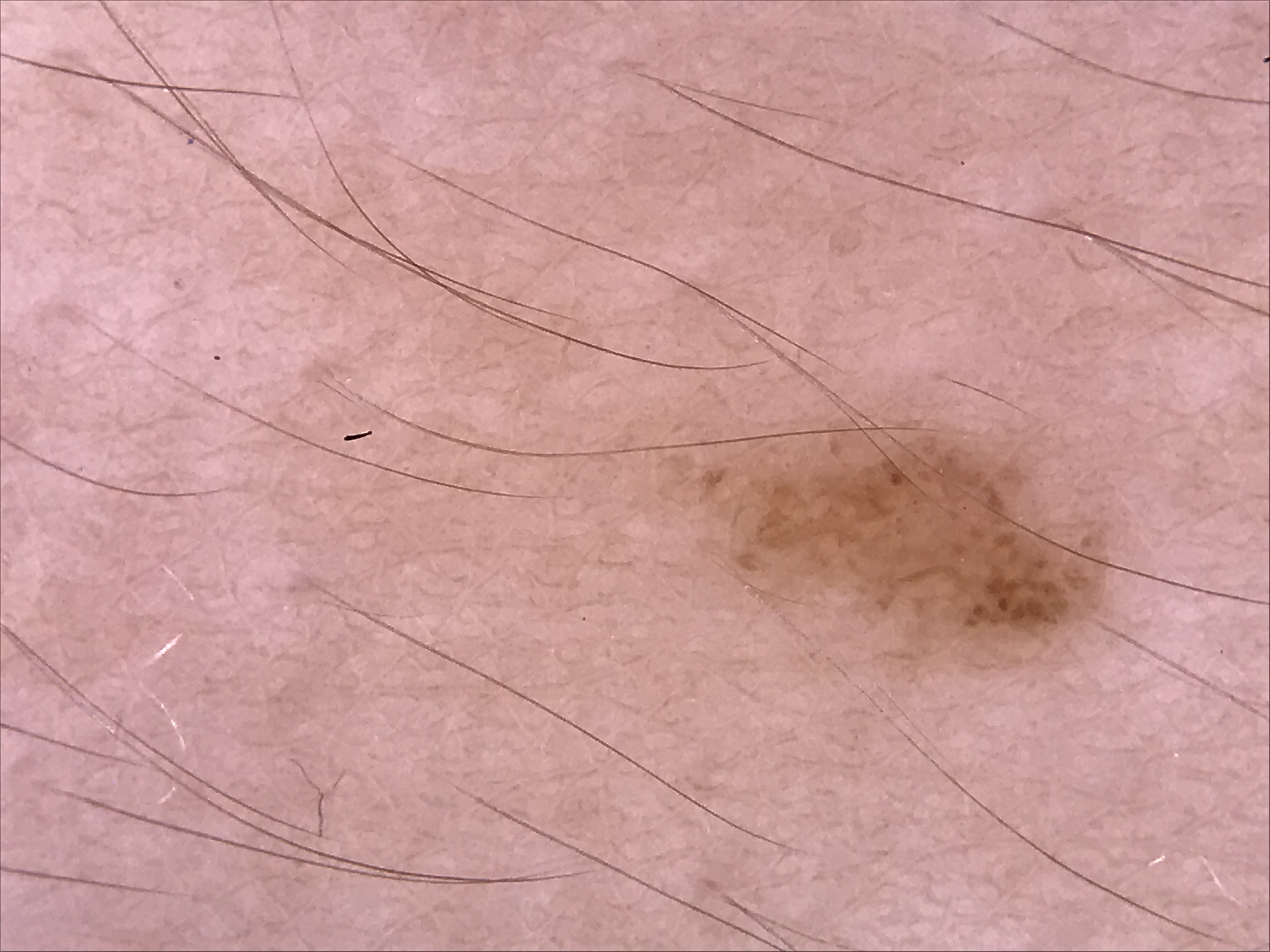A dermoscopic image of a skin lesion. The diagnostic label was a dysplastic junctional nevus.